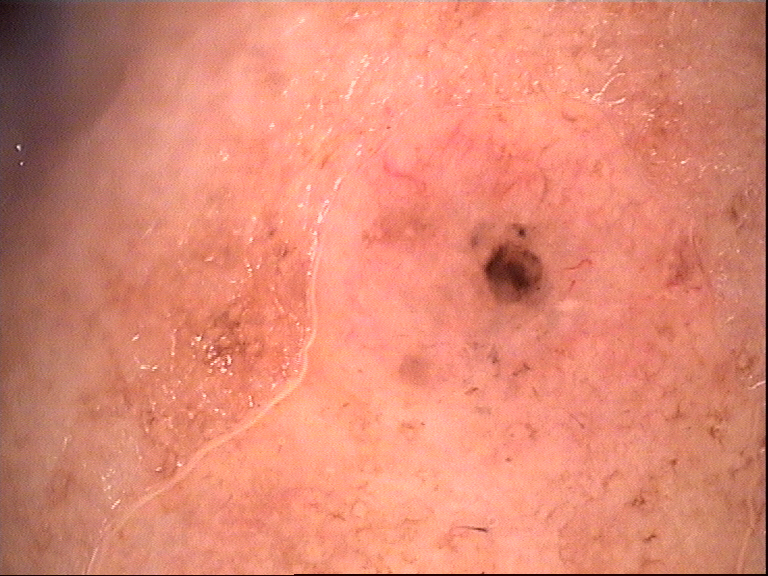label = basal cell carcinoma (biopsy-proven).